The photograph is a close-up of the affected area, the subject is a female aged 18–29 — 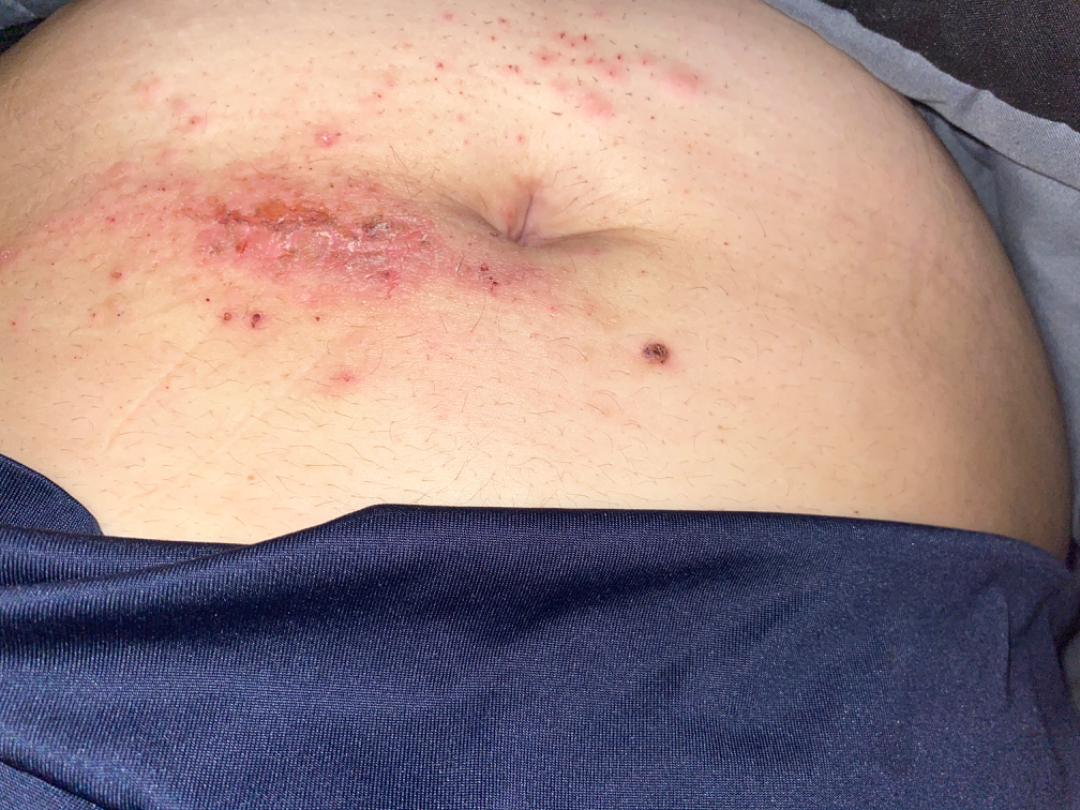Case summary:
• assessment — the favored diagnosis is Allergic Contact Dermatitis; also raised was Irritant Contact Dermatitis